A dermoscopic close-up of a skin lesion.
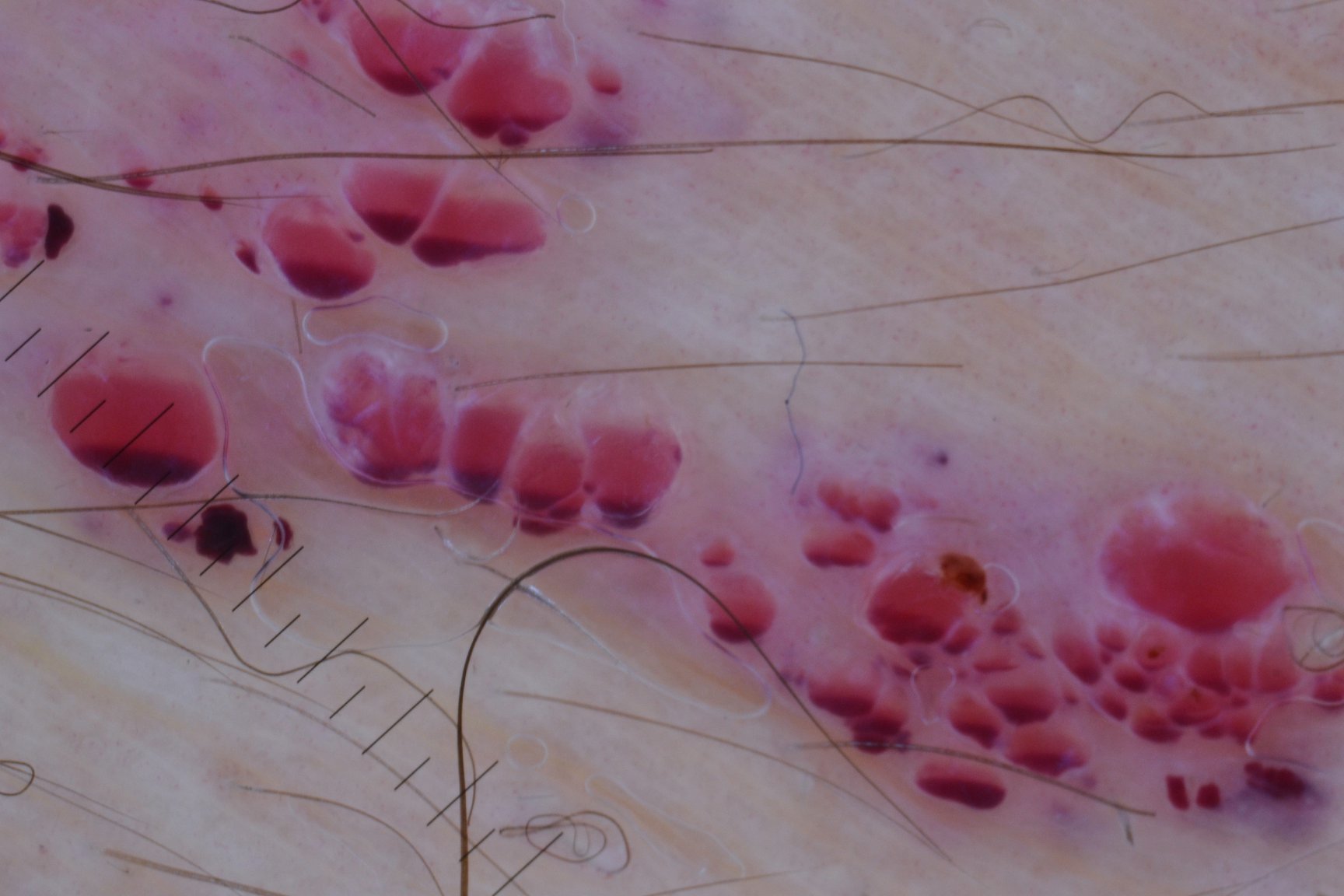Case:
- assessment: lymphangioma (expert consensus)